A dermoscopic photograph of a skin lesion:
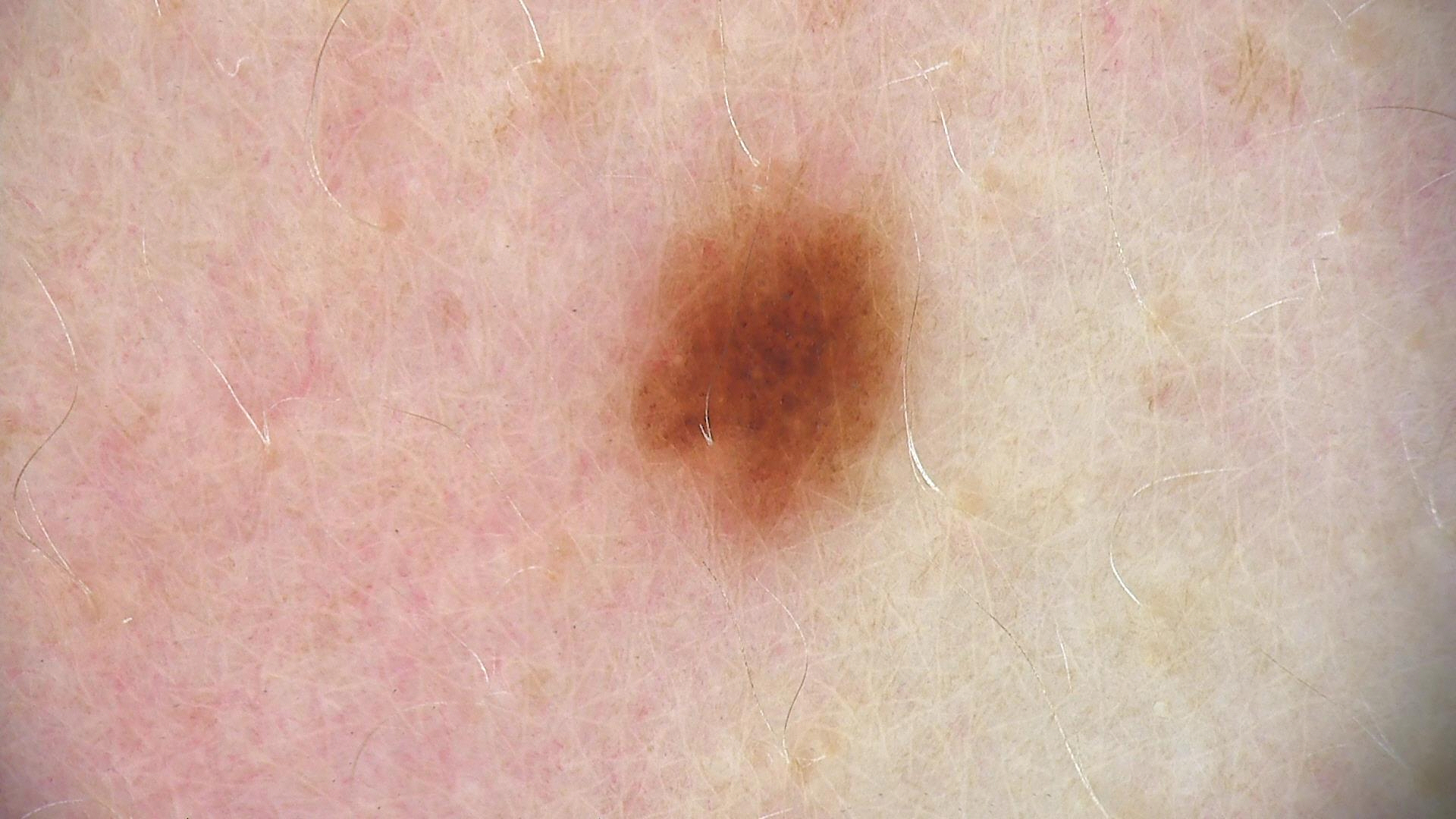Consistent with a benign lesion — a dysplastic junctional nevus.